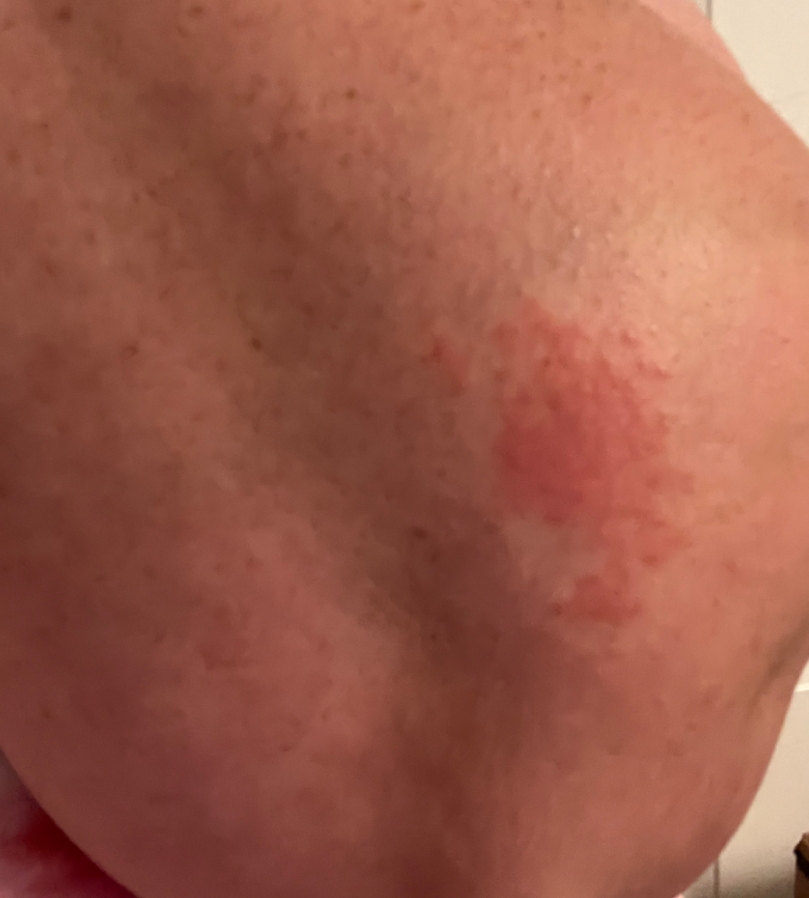Case summary:
– assessment · unable to determine
– shot type · close-up
– lesion symptoms · itching
– onset · about one day
– described texture · raised or bumpy
– location · arm
– patient's own categorization · a rash